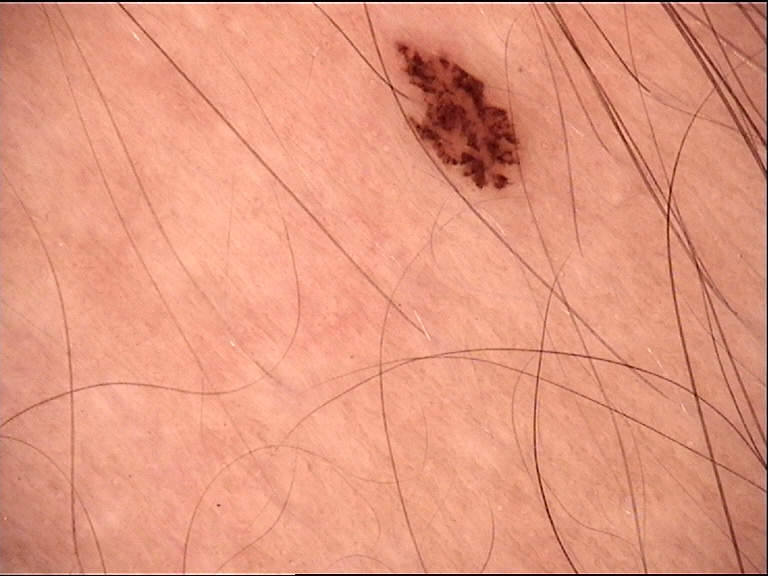modality = dermoscopy, class = dysplastic junctional nevus (expert consensus).